The photograph was taken at a distance; the patient notes the condition has been present for less than one week; the patient notes pain, bothersome appearance, darkening, itching and burning; self-categorized by the patient as a rash; the lesion is described as raised or bumpy:
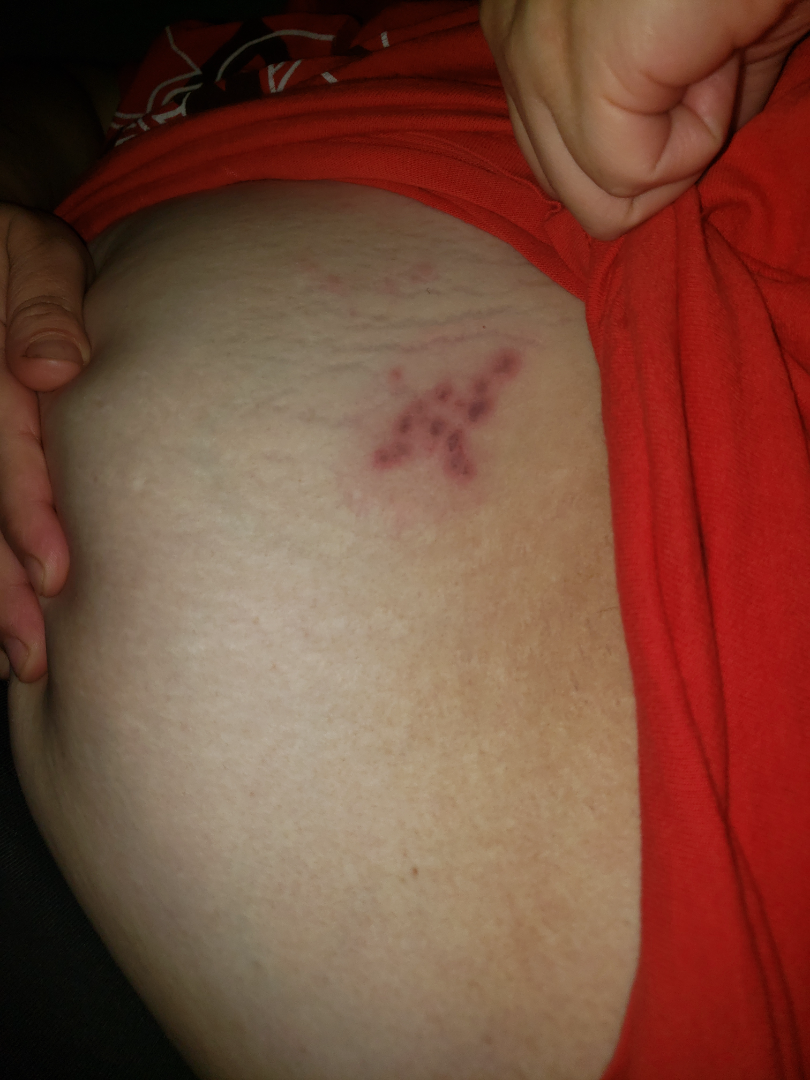| field | value |
|---|---|
| differential | one reviewing dermatologist: the leading consideration is Herpes Simplex; possibly Herpes Zoster |